The condition has been present for less than one week; a close-up photograph; the front of the torso is involved; the contributor is 70–79, female; self-categorized by the patient as a rash; the lesion is described as raised or bumpy.
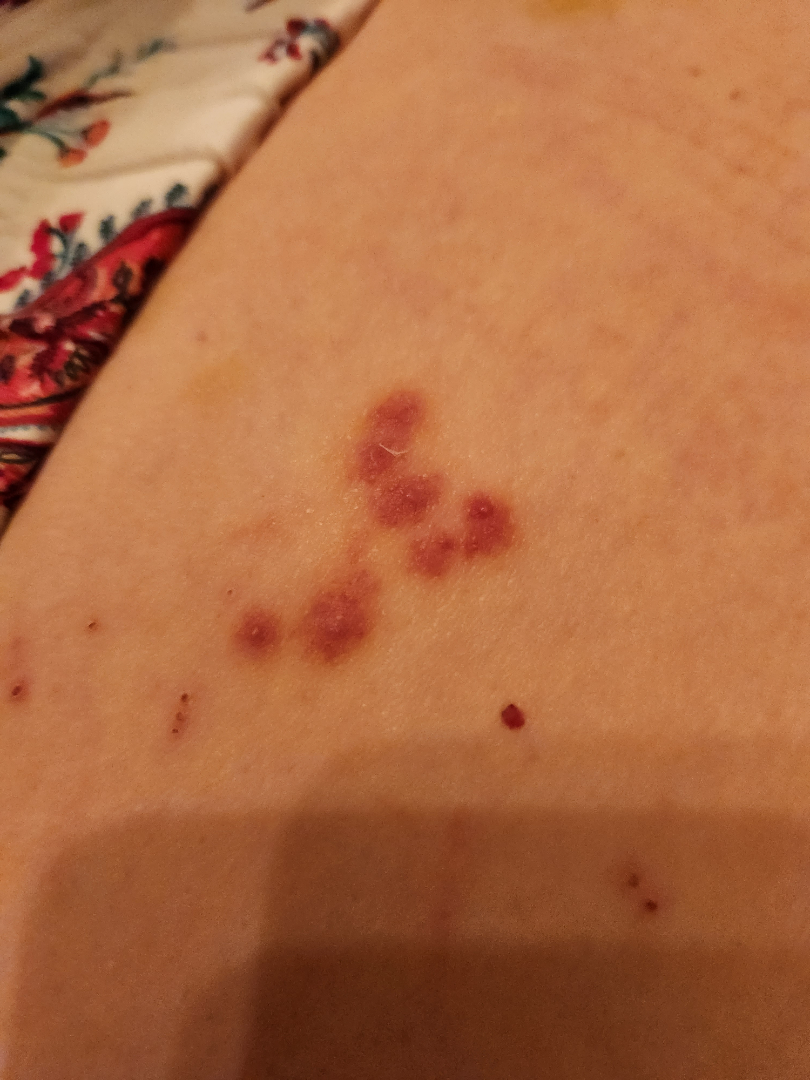On remote dermatologist review: the leading consideration is Herpes Simplex; also consider Insect Bite; lower on the differential is Superficial wound of body region.